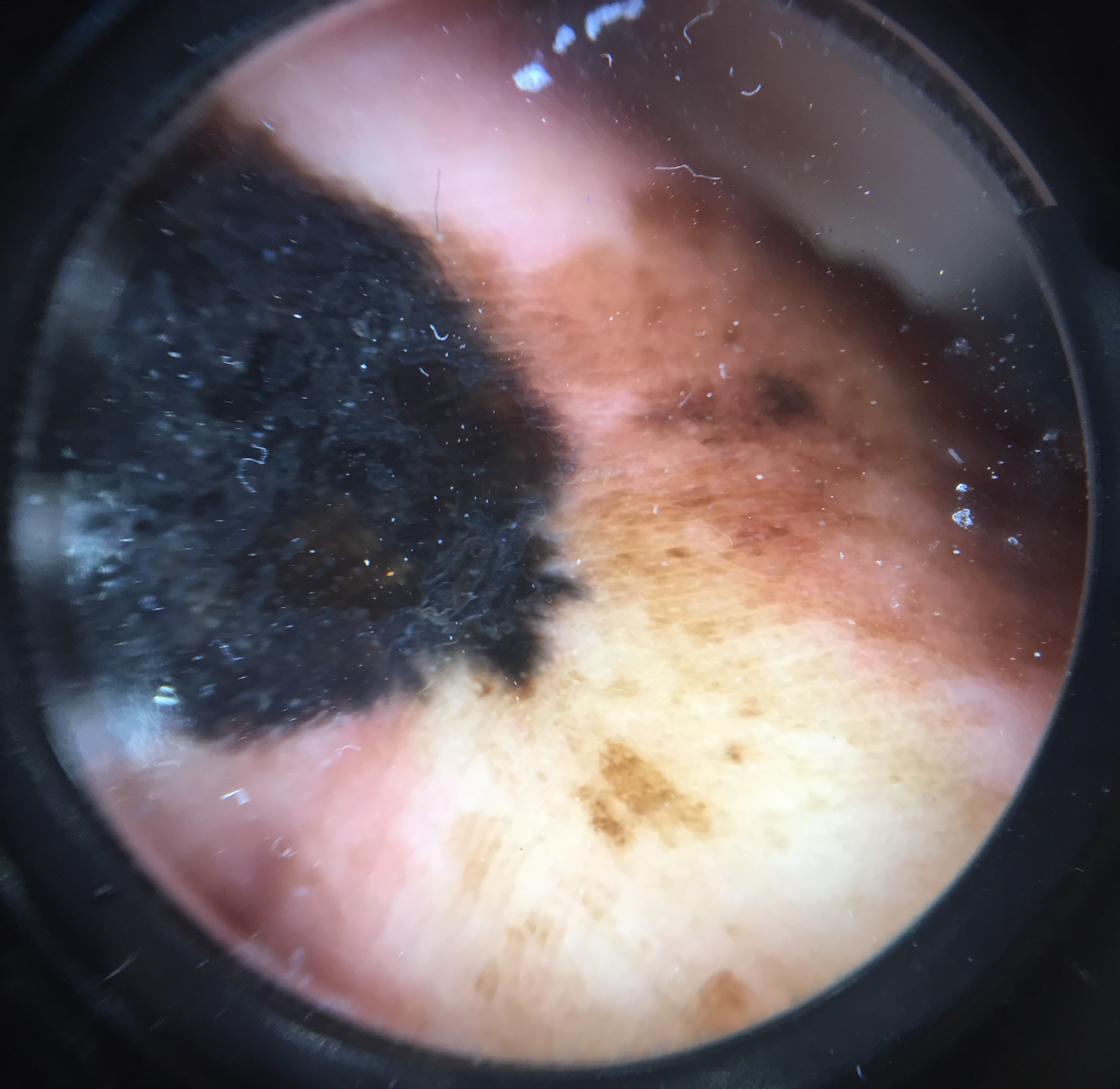Summary: A dermoscopic photograph of a skin lesion. Conclusion: Histopathology confirmed an acral lentiginous melanoma.